Collected as part of a research study, without a referral diagnosis · a male patient 89 years of age · a dermoscopic image of a skin lesion: 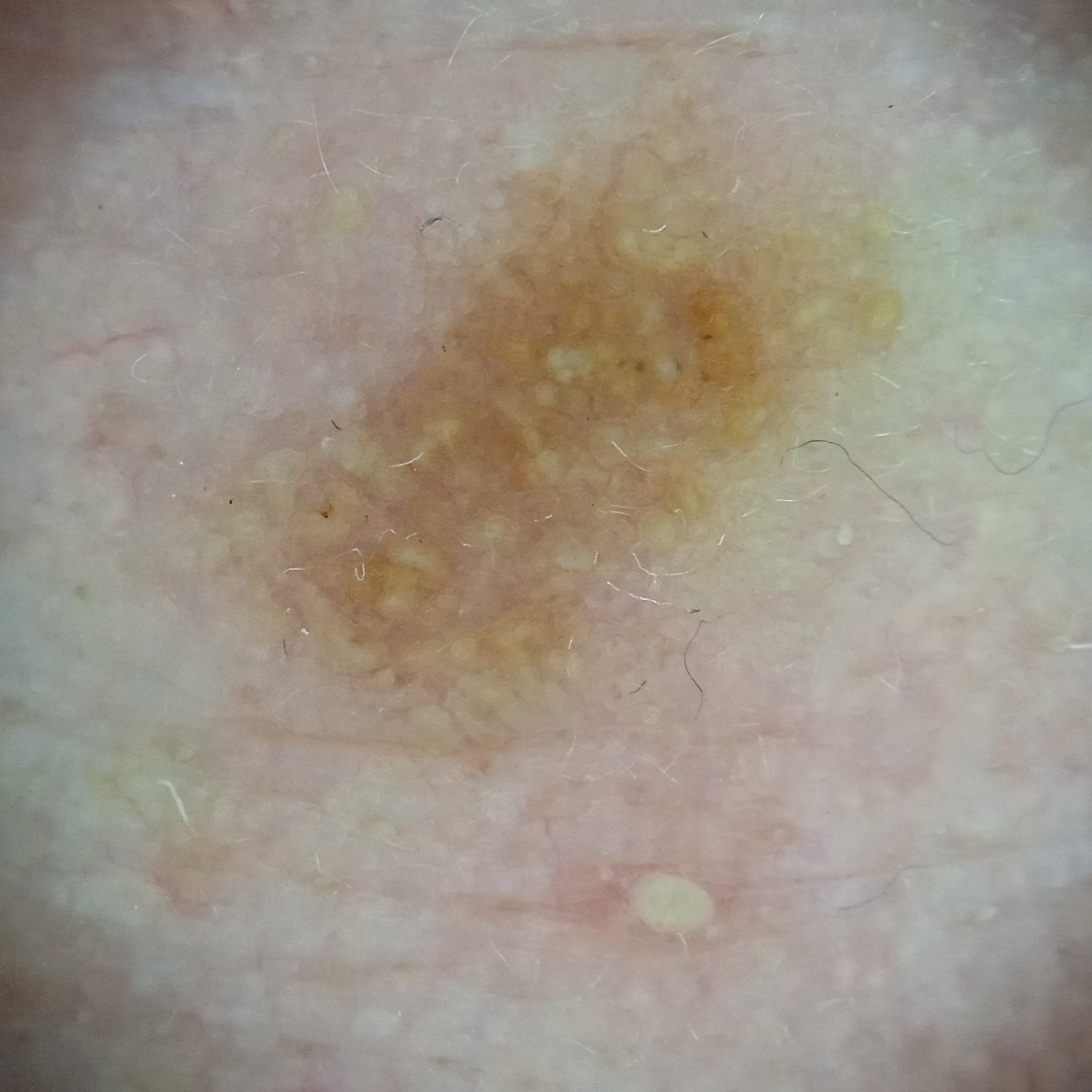size = 6.4 mm
diagnostic label = actinic keratosis (dermatologist consensus)